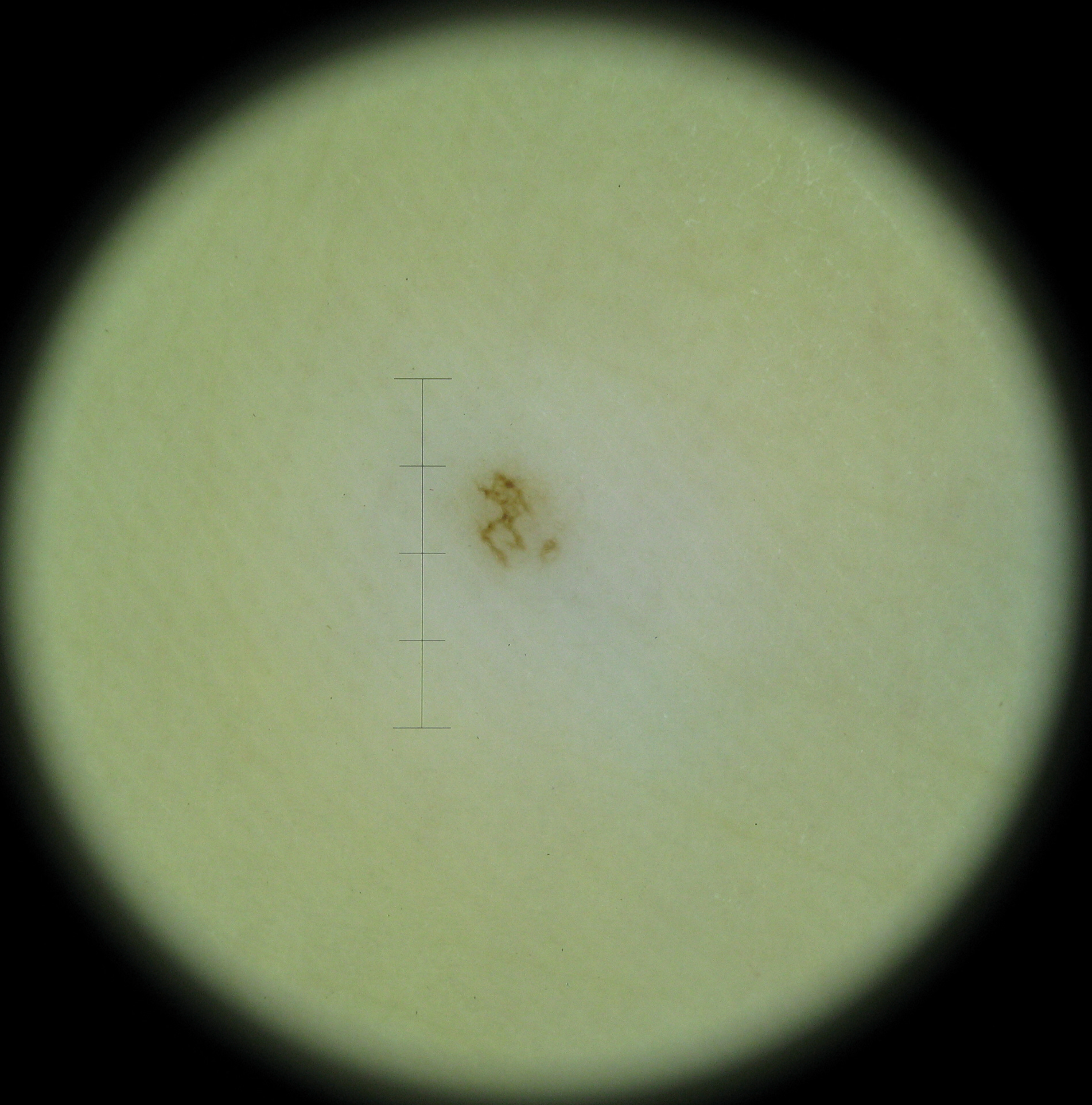Case: The morphology is that of a banal lesion. Impression: Classified as an acral junctional nevus.